A female patient in their 70s · history notes prior malignancy (patient or family), pesticide exposure, prior skin cancer (patient or family), no tobacco use, and no alcohol use · a clinical close-up photograph of a skin lesion · recorded as skin type II — 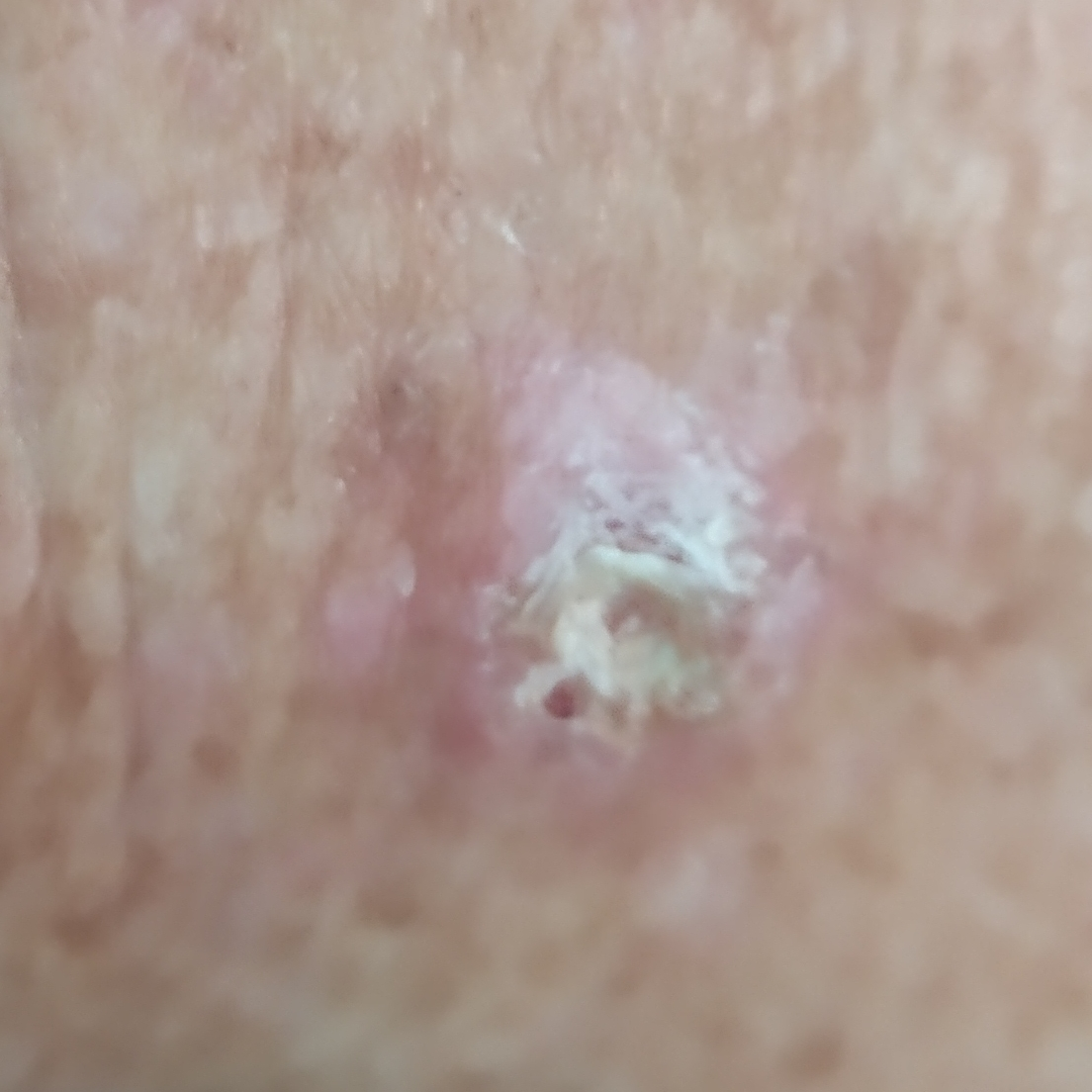Located on an arm.
The lesion is roughly 11 by 10 mm.
Per patient report, the lesion is elevated and itches, but does not hurt.
Biopsy-confirmed as an actinic keratosis.